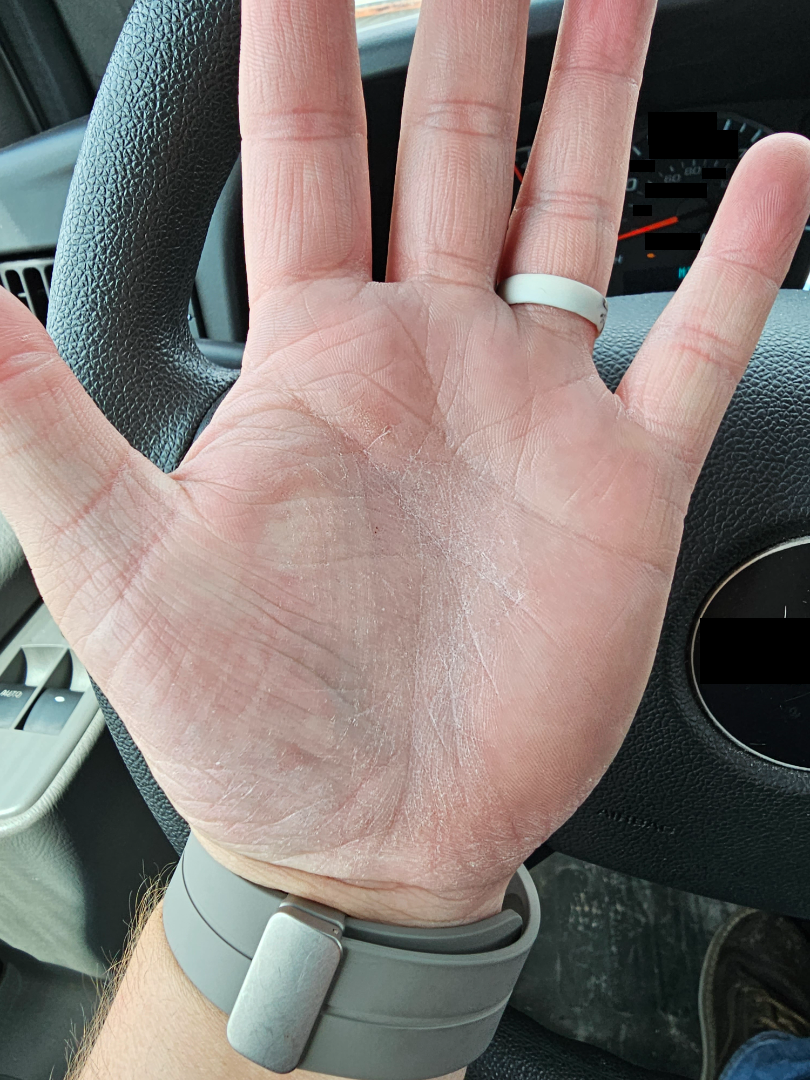clinical impression=single-reviewer assessment: Tinea, Eczema and Irritant Contact Dermatitis were considered with similar weight.